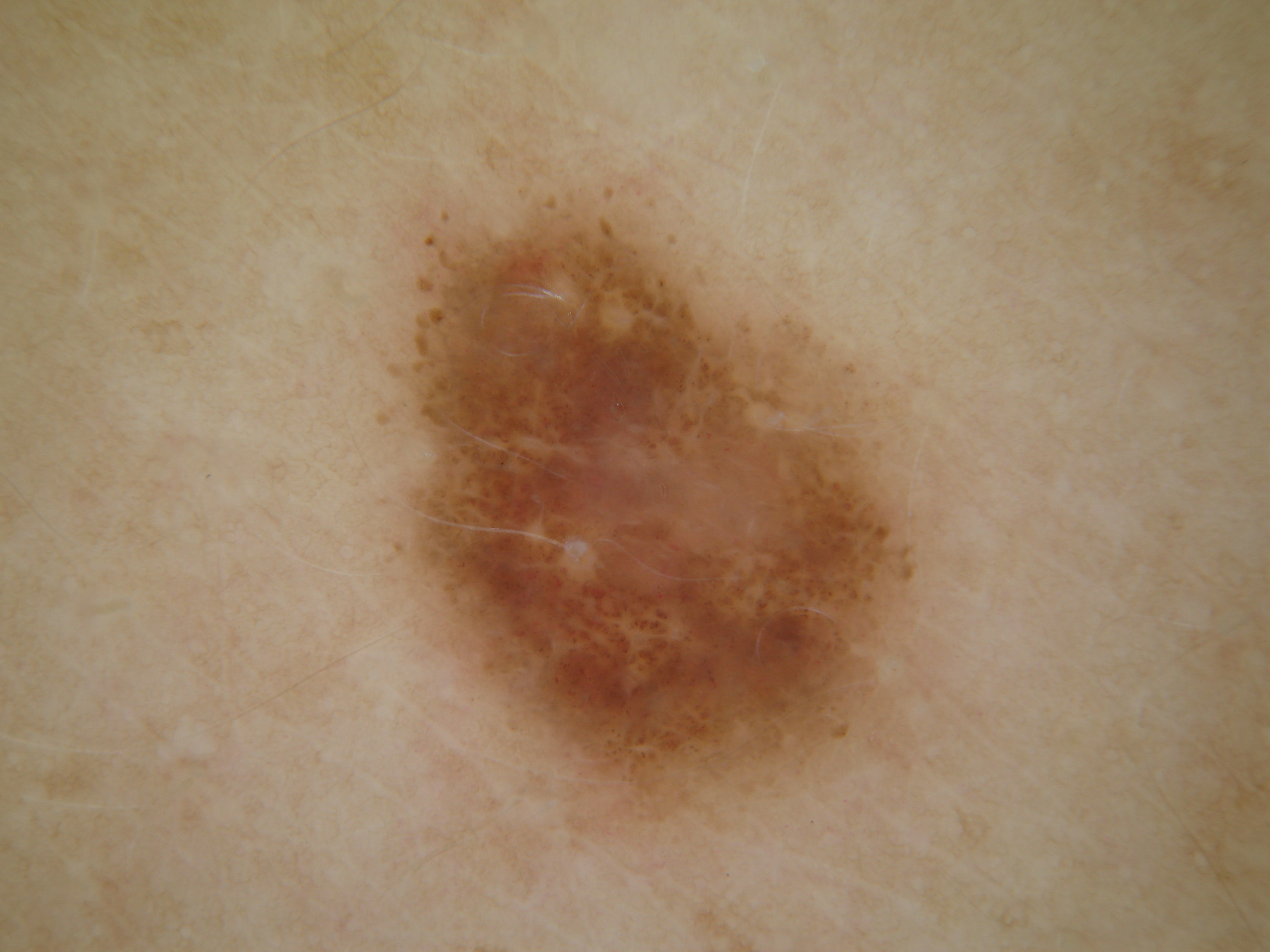{"image": {"modality": "dermoscopy"}, "lesion_location": {"bbox_xyxy": [379, 157, 973, 876]}, "dermoscopic_features": {"present": ["globules", "negative network"], "absent": ["streaks", "pigment network", "milia-like cysts"]}, "lesion_extent": {"approx_field_fraction_pct": 23}, "diagnosis": {"name": "melanocytic nevus", "malignancy": "benign", "lineage": "melanocytic", "provenance": "clinical"}}